The lesion involves the leg, the lesion is described as rough or flaky, this image was taken at a distance, the patient notes the condition has been present for one to four weeks.
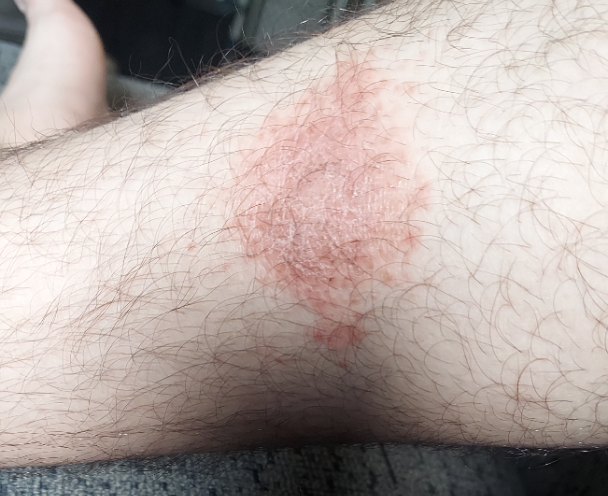Assessment: On photographic review by a dermatologist, in keeping with Eczema.